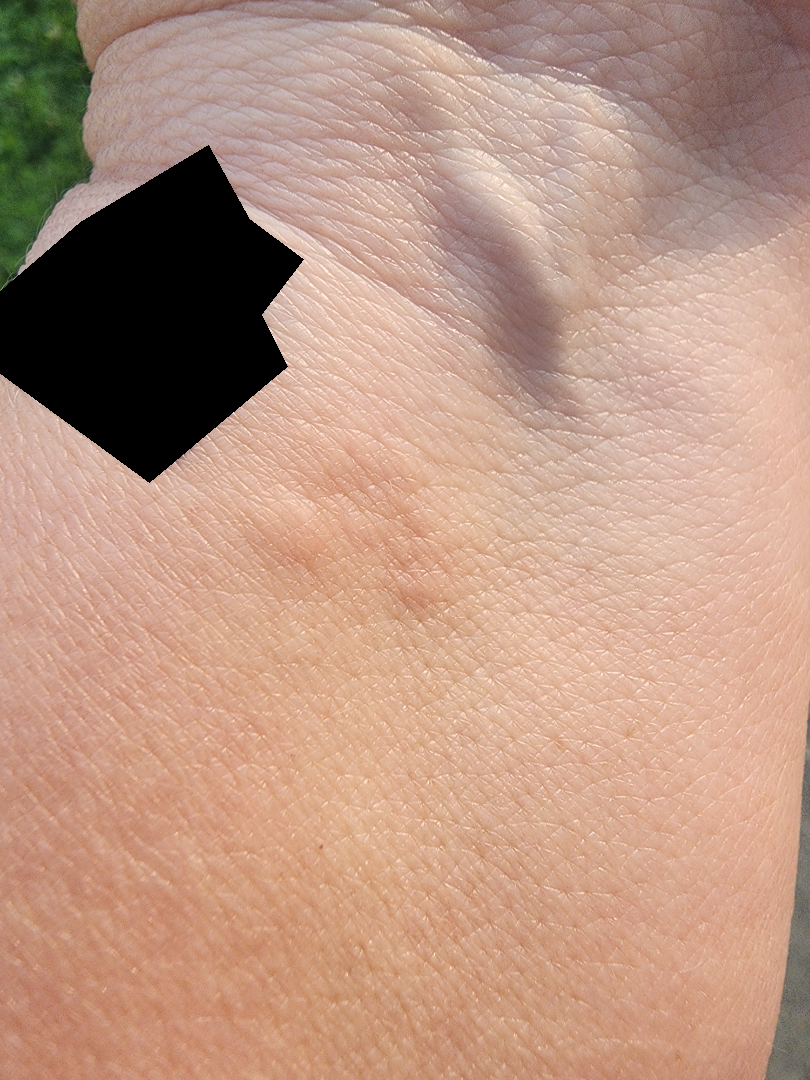Skin tone: Fitzpatrick phototype II; human graders estimated a Monk skin tone scale of 2.
The photograph is a close-up of the affected area.
Texture is reported as raised or bumpy.
The subject is a female aged 50–59.
The arm is involved.
No relevant lesion symptoms reported.
Urticaria (primary); Allergic Contact Dermatitis (possible); Herpes Simplex (remote).